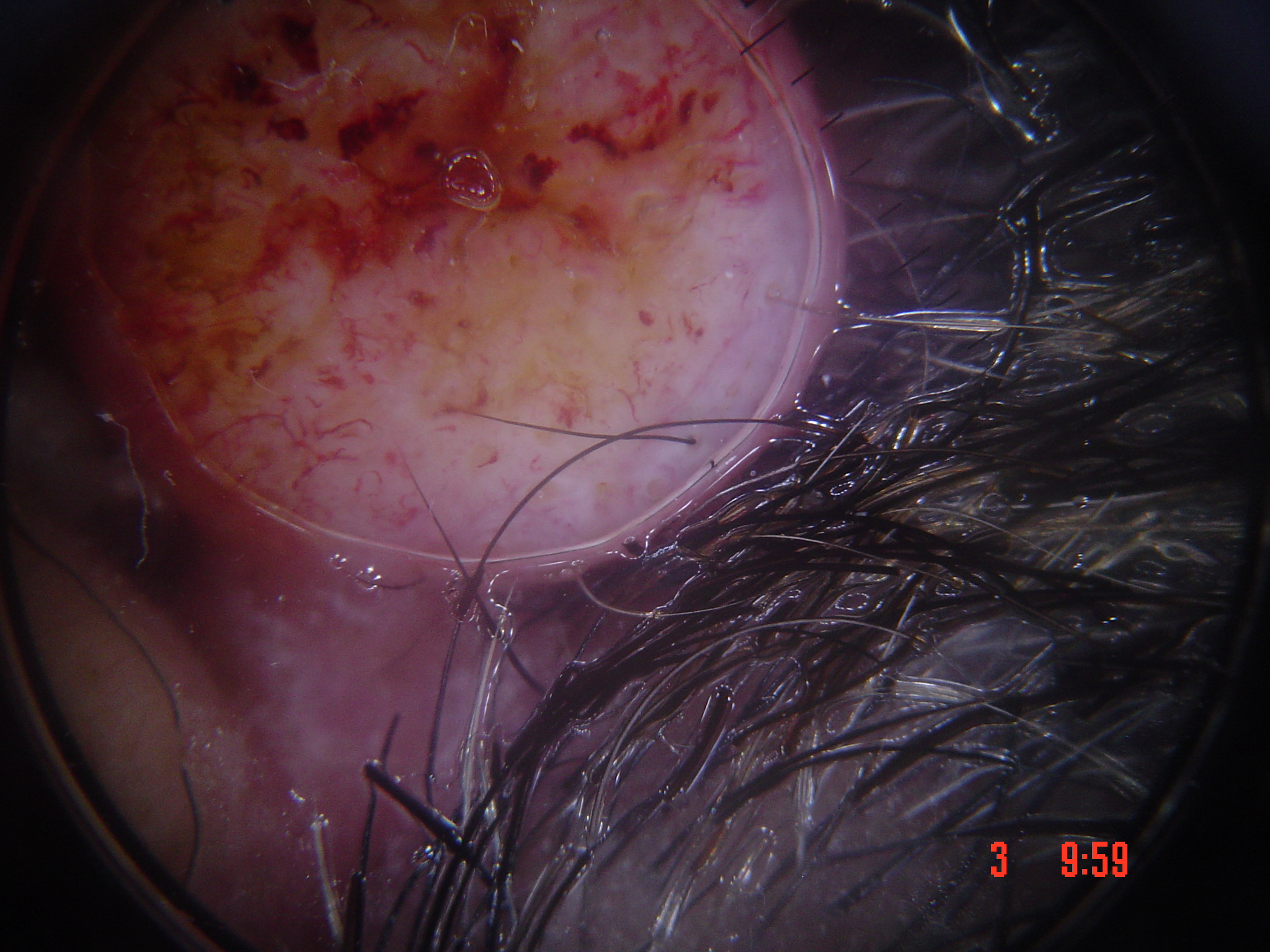lesion_type:
  main_class: keratinocytic
diagnosis:
  name: squamous cell carcinoma
  code: scc
  malignancy: malignant
  super_class: non-melanocytic
  confirmation: histopathology